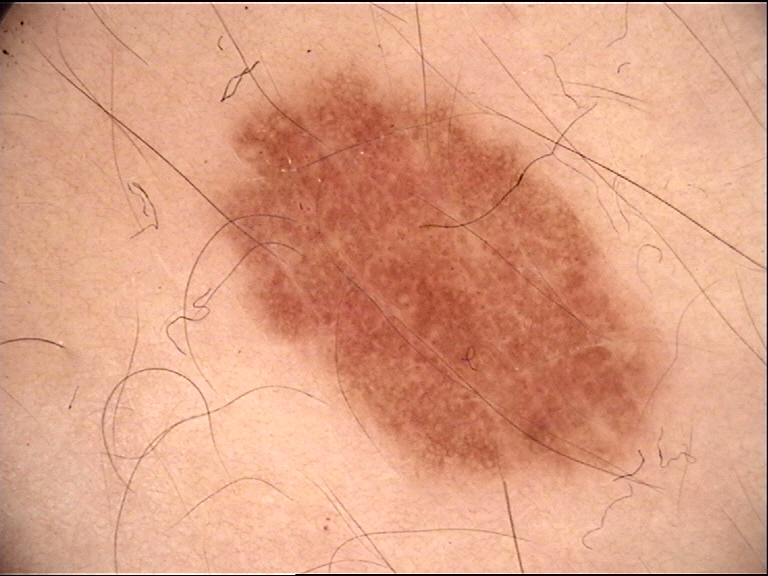Dermoscopy of a skin lesion. The diagnostic label was a benign lesion — a dysplastic junctional nevus.